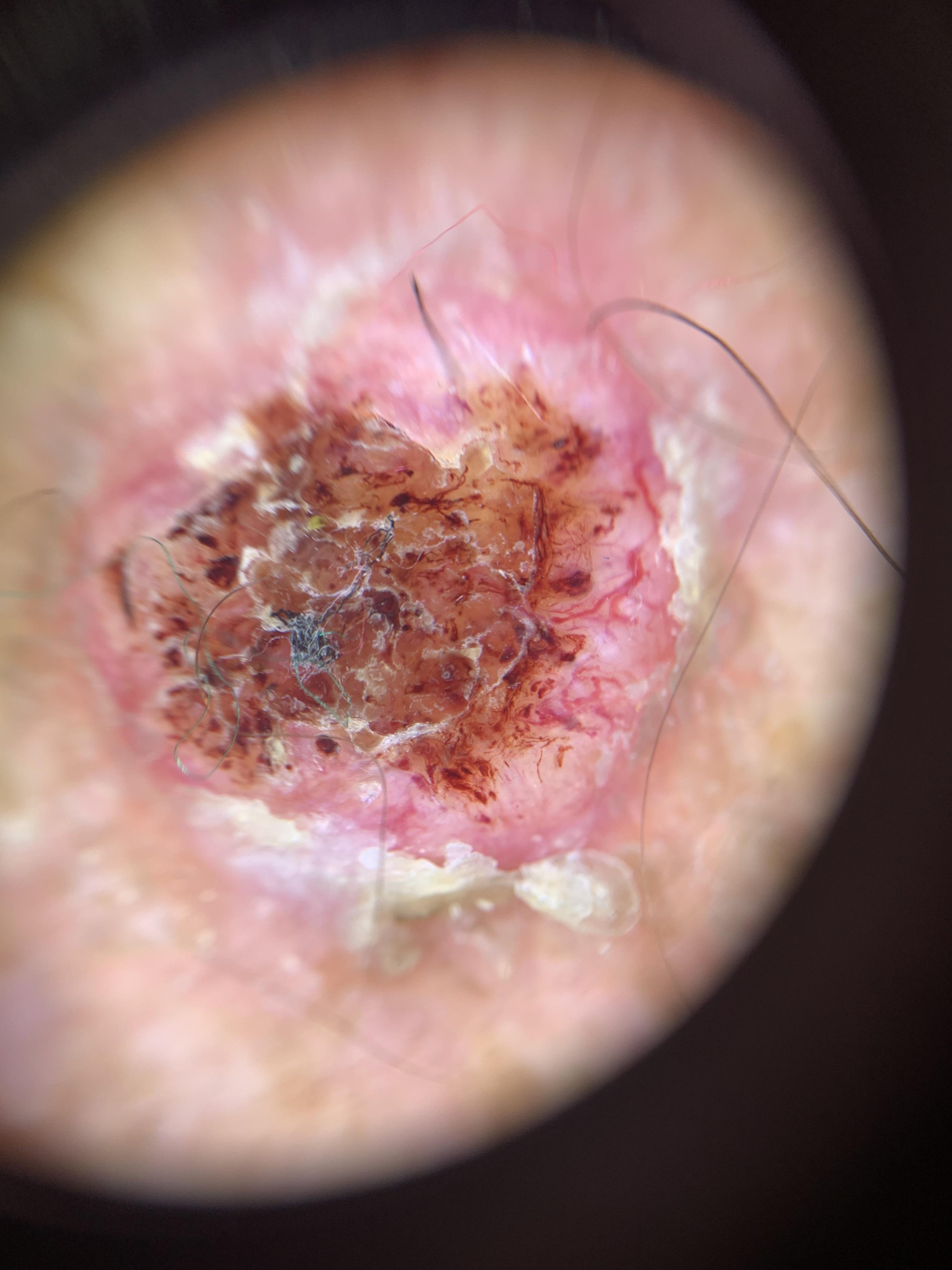{"patient": {"age_approx": "85+", "sex": "male"}, "image": "contact-polarized dermoscopy", "diagnosis": {"name": "Squamous cell carcinoma", "malignancy": "malignant", "confirmation": "histopathology", "lineage": "epidermal"}}